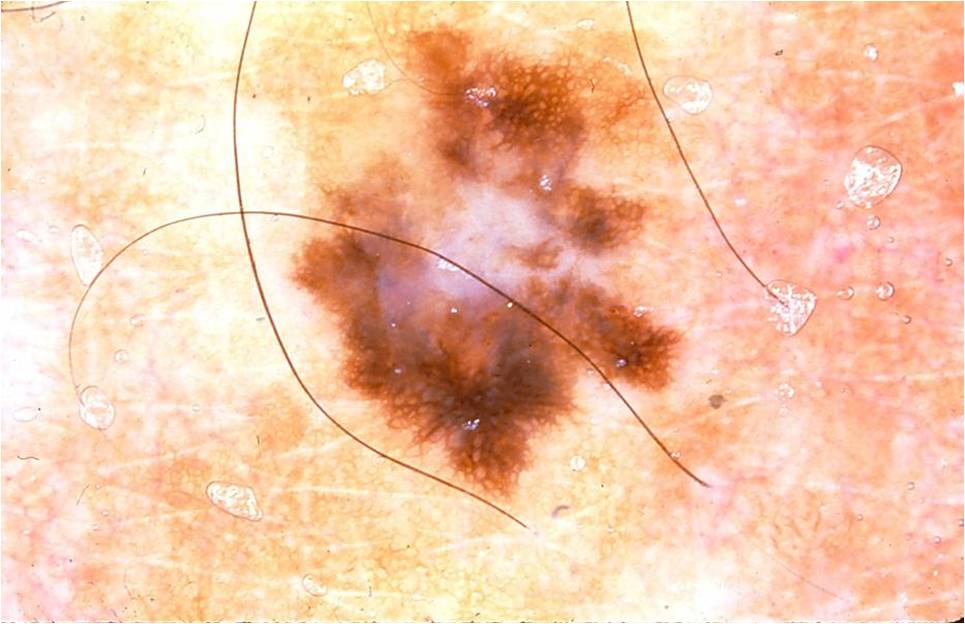Dermoscopy of a skin lesion.
A male subject, in their 40s.
Dermoscopic review identifies pigment network, with no streaks, milia-like cysts, globules, or negative network.
In (x1, y1, x2, y2) order, lesion location: 233, 6, 693, 500.
Confirmed on histopathology as a melanoma.